A dermoscopy image of a single skin lesion: 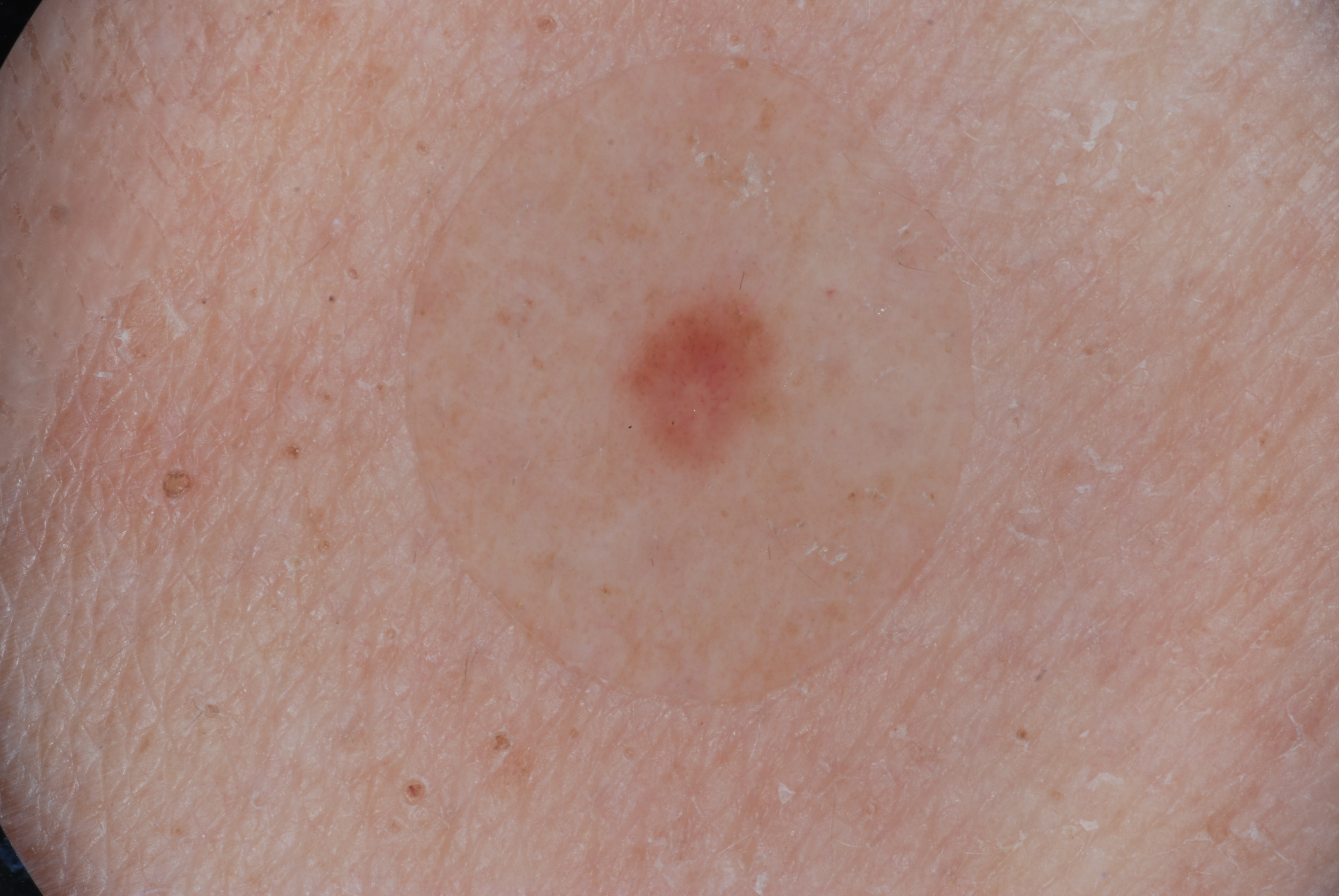Q: Where is the lesion in the image?
A: x1=593 y1=261 x2=797 y2=507
Q: Which assessed dermoscopic features were absent?
A: streaks, negative network, milia-like cysts, and pigment network
Q: How large is the lesion within the image?
A: small
Q: What did the assessment conclude?
A: a melanocytic nevus